Dermoscopy of a skin lesion.
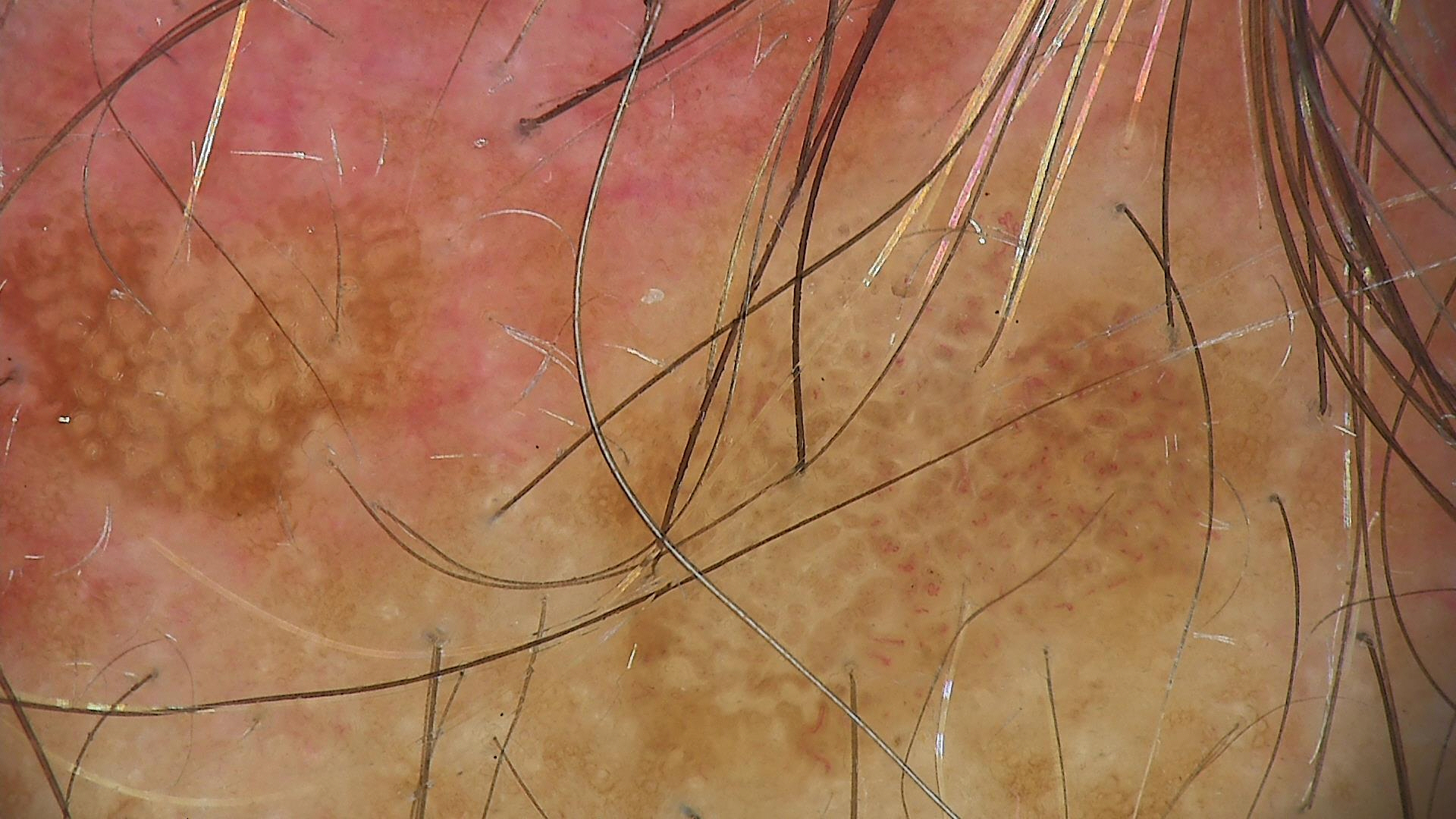Q: What is the lesion category?
A: keratinocytic
Q: What was the diagnostic impression?
A: seborrheic keratosis (expert consensus)